The arm is involved. The patient described the issue as a rash. The photograph was taken at a distance. The contributor is male. Reported duration is one to four weeks. The contributor reports the lesion is raised or bumpy. The lesion is associated with bothersome appearance. Skin tone: Fitzpatrick III — 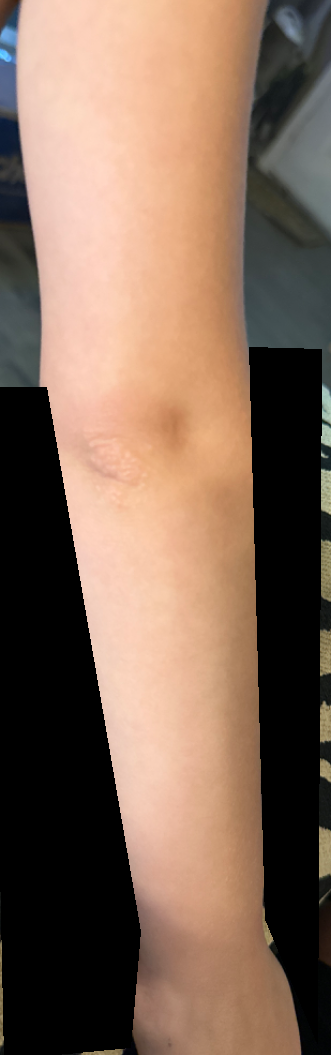| key | value |
|---|---|
| dermatologist impression | Epidermal nevus (0.33); Verruca vulgaris (0.33); Psoriasis (0.33) |